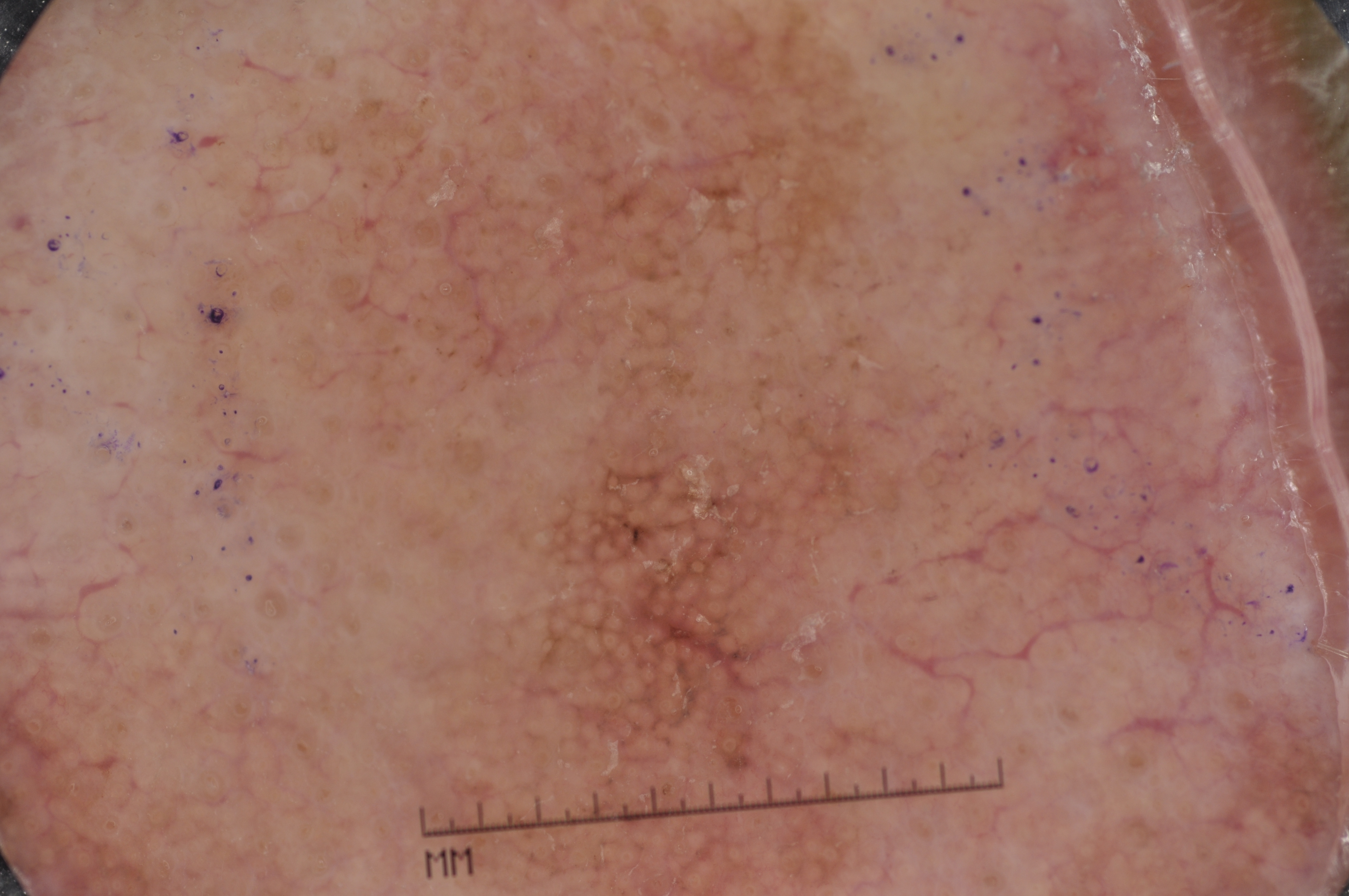Q: What are the patient's age and sex?
A: male, aged approximately 75
Q: What kind of image is this?
A: dermatoscopic image of a skin lesion
Q: How large is the lesion within the image?
A: large
Q: What dermoscopic features are not present?
A: pigment network, negative network, streaks, and milia-like cysts
Q: Where is the lesion located?
A: x1=195 y1=2 x2=1058 y2=895
Q: What is this lesion?
A: a melanoma